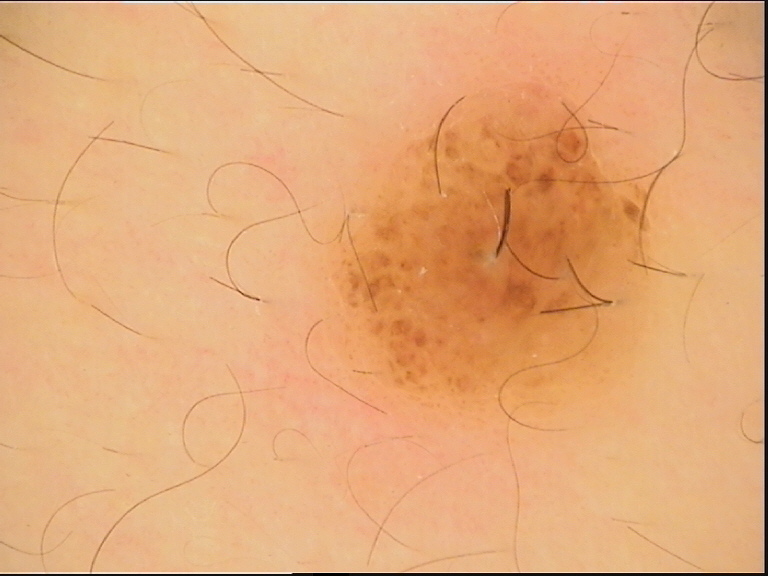A skin lesion imaged with a dermatoscope. The architecture is that of a banal lesion. Consistent with a compound nevus.